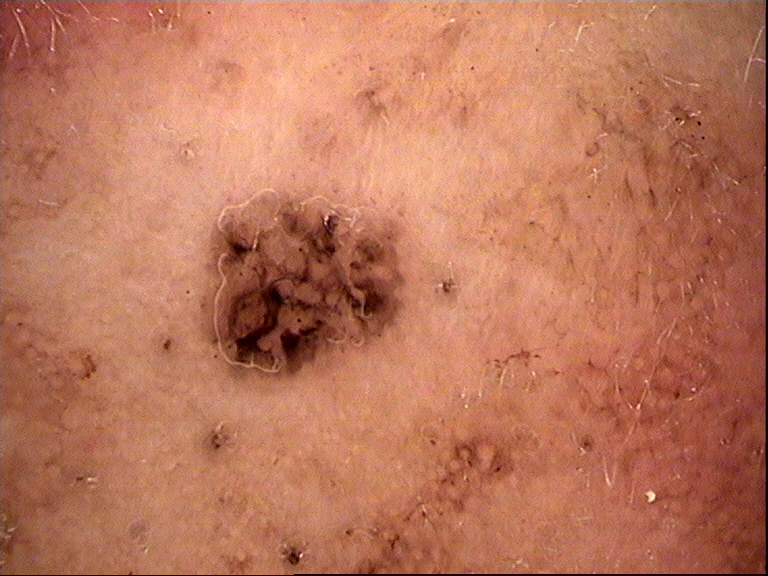Findings:
– modality · dermatoscopy
– lesion type · keratinocytic
– label · basal cell carcinoma (biopsy-proven)